The patient says their skin reddens painfully with sun exposure · a dermoscopic image of a skin lesion · acquired for a research image collection, with no referral diagnosis · a female patient 81 years of age · a moderate number of moles by the patient's own estimate.
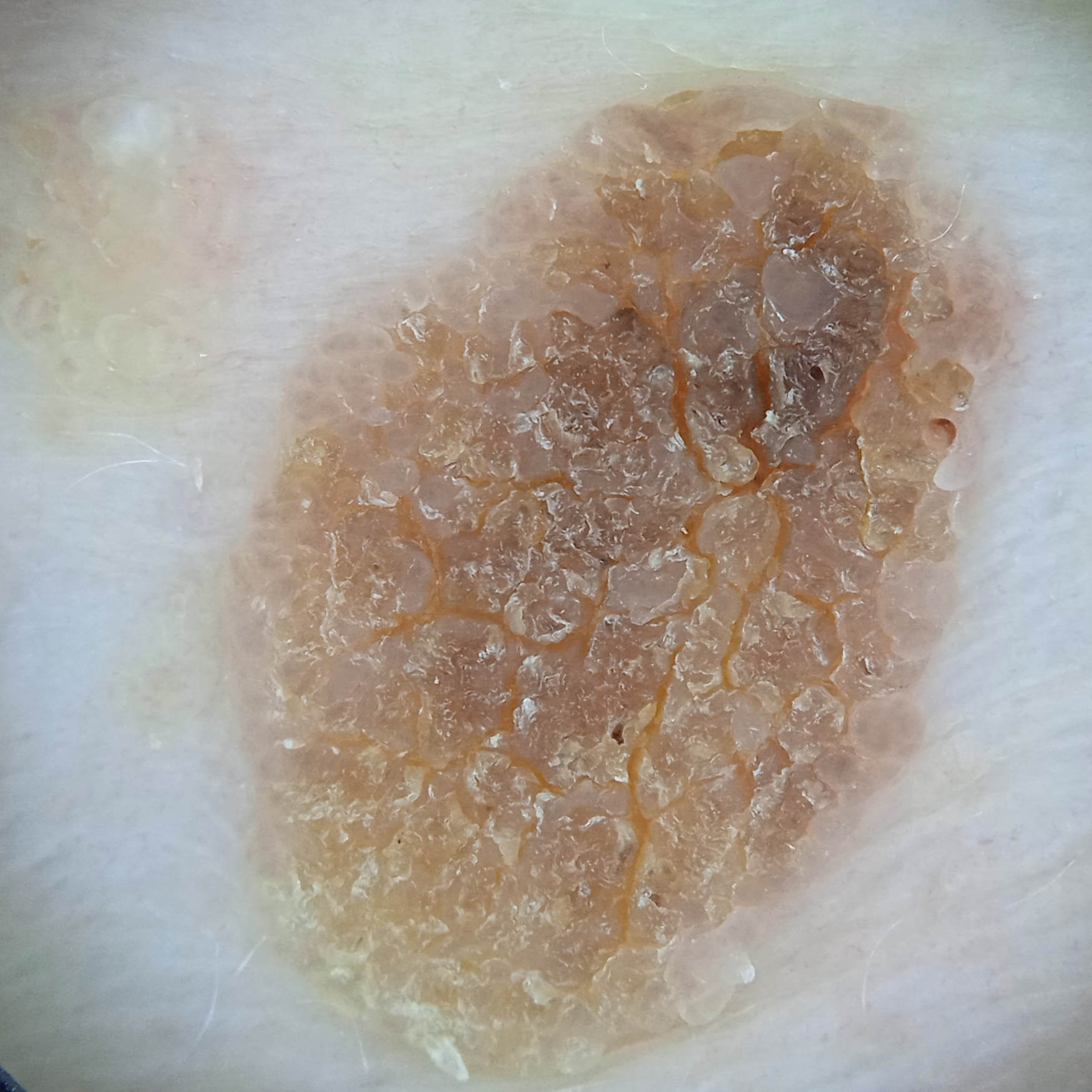The lesion involves the torso. Measuring roughly 12.2 mm. Dermatologist review favored a seborrheic keratosis.